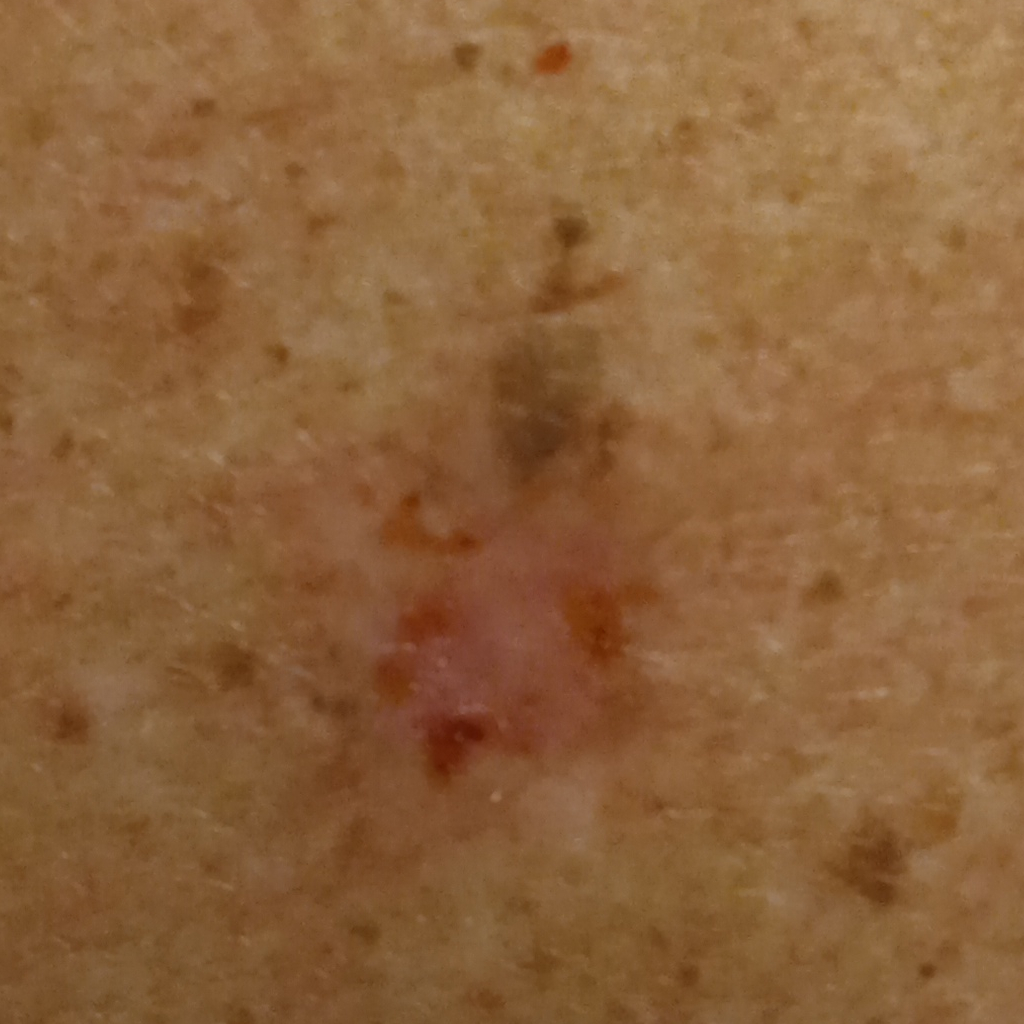By self-report, a personal history of cancer and a family history of skin cancer. The referring clinician suspected basal cell carcinoma. A male subject age 81. The patient describes having few moles overall. The patient says their skin reddens with sun exposure. A clinical photograph showing a skin lesion. Located on the back. The lesion is about 12.6 mm across. Histopathology confirmed a basal cell carcinoma, following excision, with a measured tumor thickness of 3 mm.